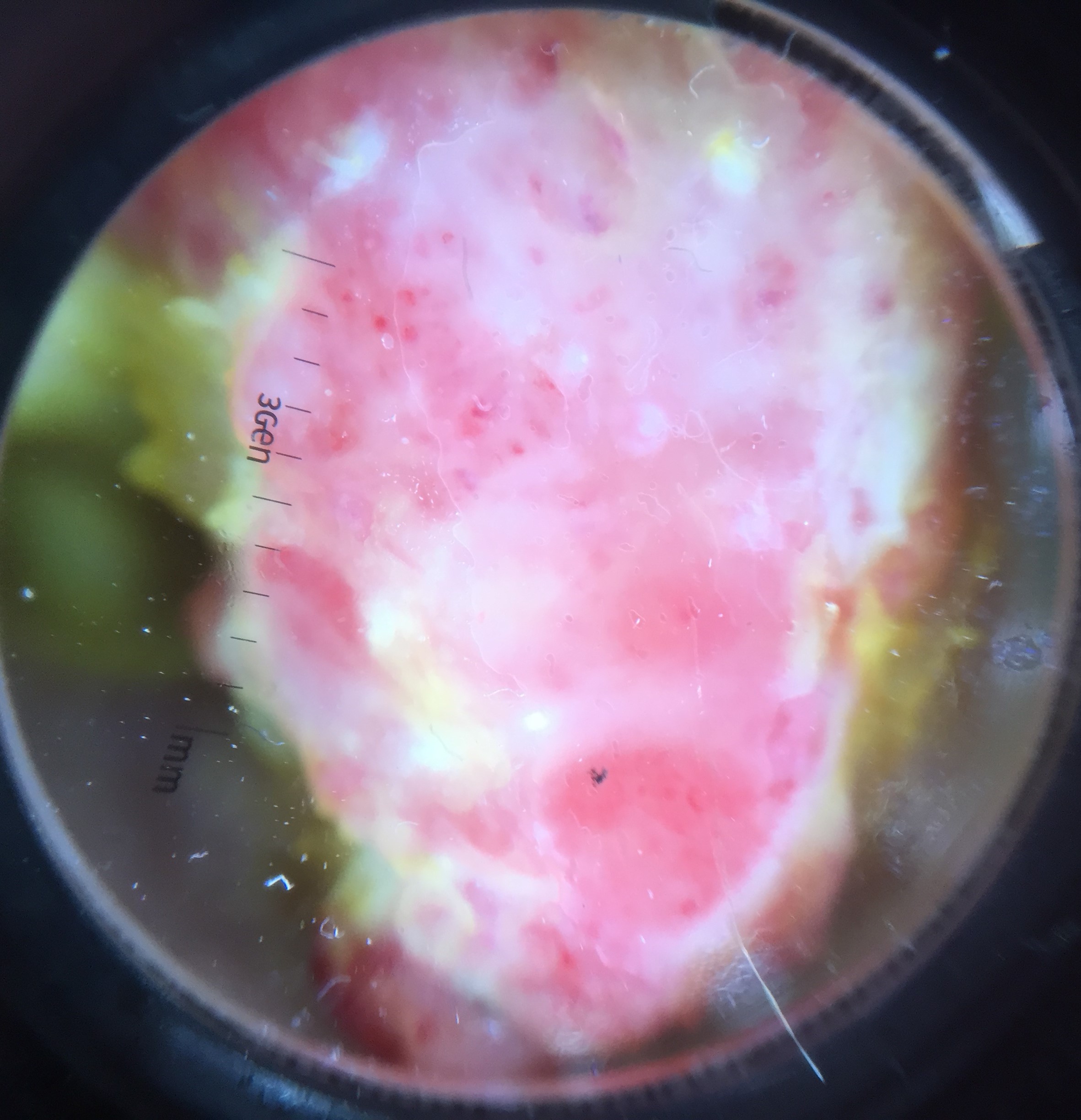image — dermoscopy
pathology — acral nodular melanoma (biopsy-proven)